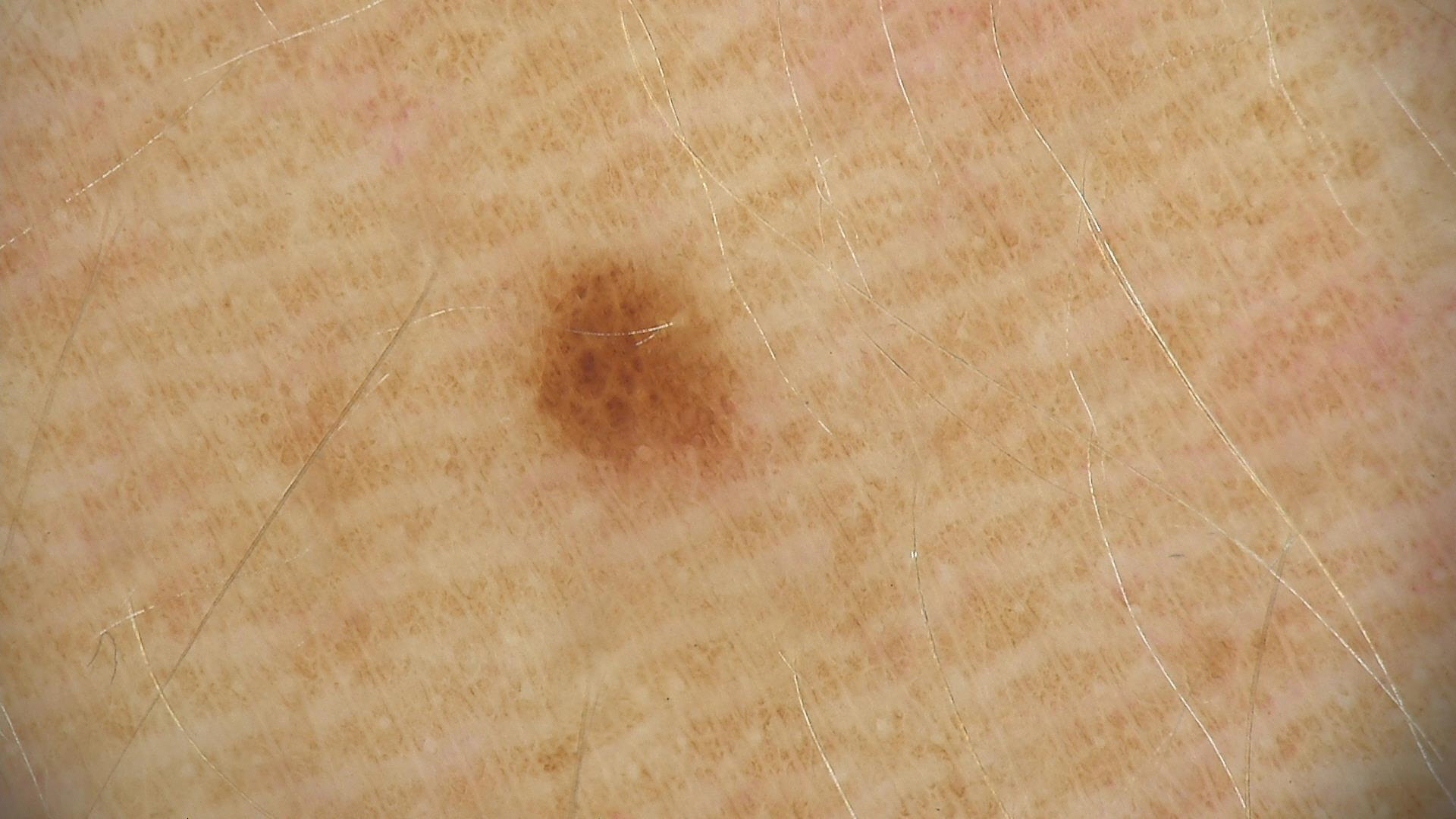• label: dysplastic junctional nevus (expert consensus)